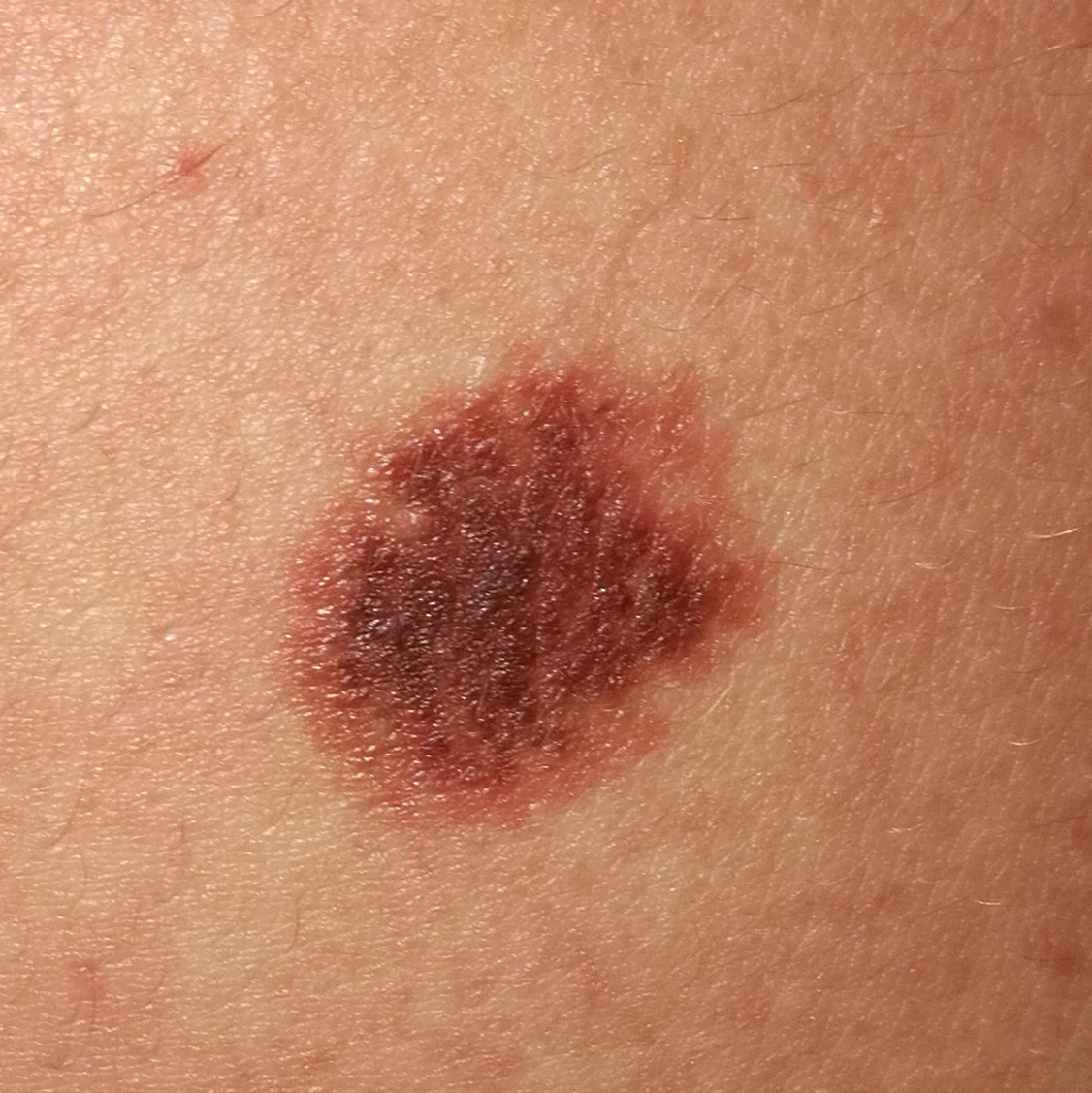Notes:
- subject: 23 years old
- modality: clinical photograph
- anatomic site: the back
- patient-reported symptoms: growth, change in appearance, itching
- diagnosis: nevus (clinical consensus)